This is a dermoscopic photograph of a skin lesion · a female subject roughly 40 years of age.
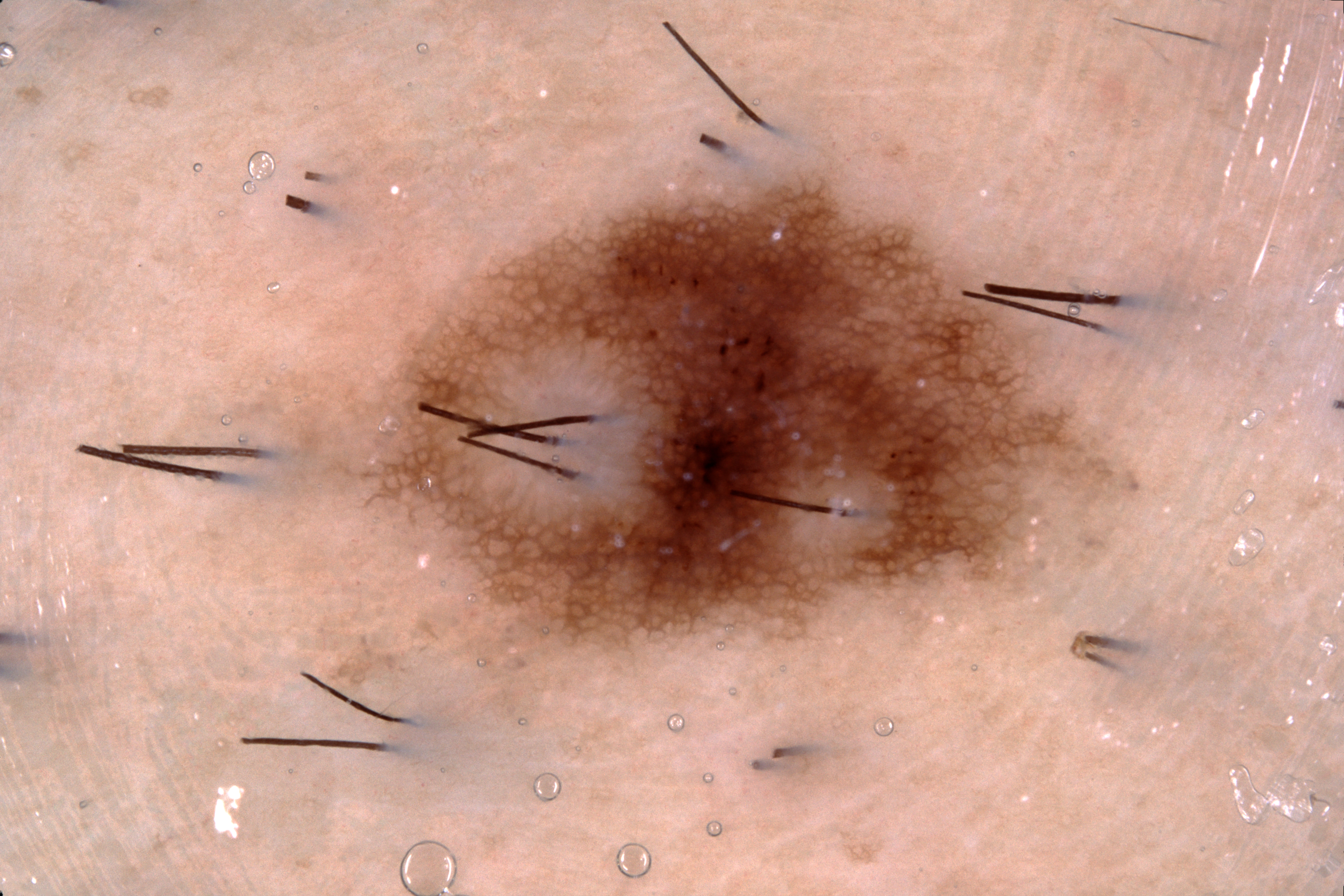extent — moderate
features — pigment network; absent: streaks, negative network, and milia-like cysts
bounding box — 378 182 1102 644
assessment — a melanocytic nevus